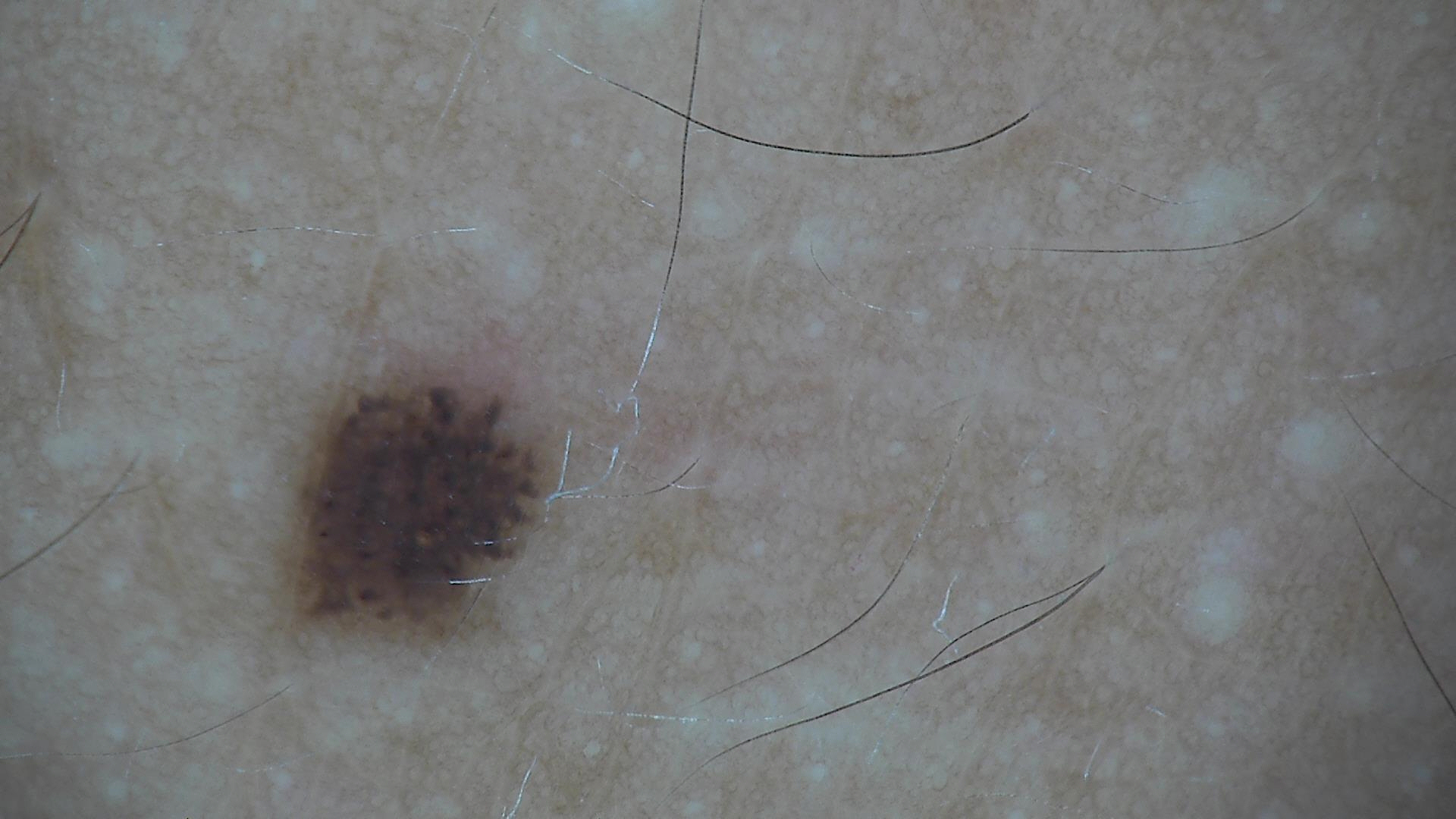<dermoscopy>
<diagnosis>
<name>dysplastic junctional nevus</name>
<code>jd</code>
<malignancy>benign</malignancy>
<super_class>melanocytic</super_class>
<confirmation>expert consensus</confirmation>
</diagnosis>
</dermoscopy>